A skin lesion imaged with a dermatoscope.
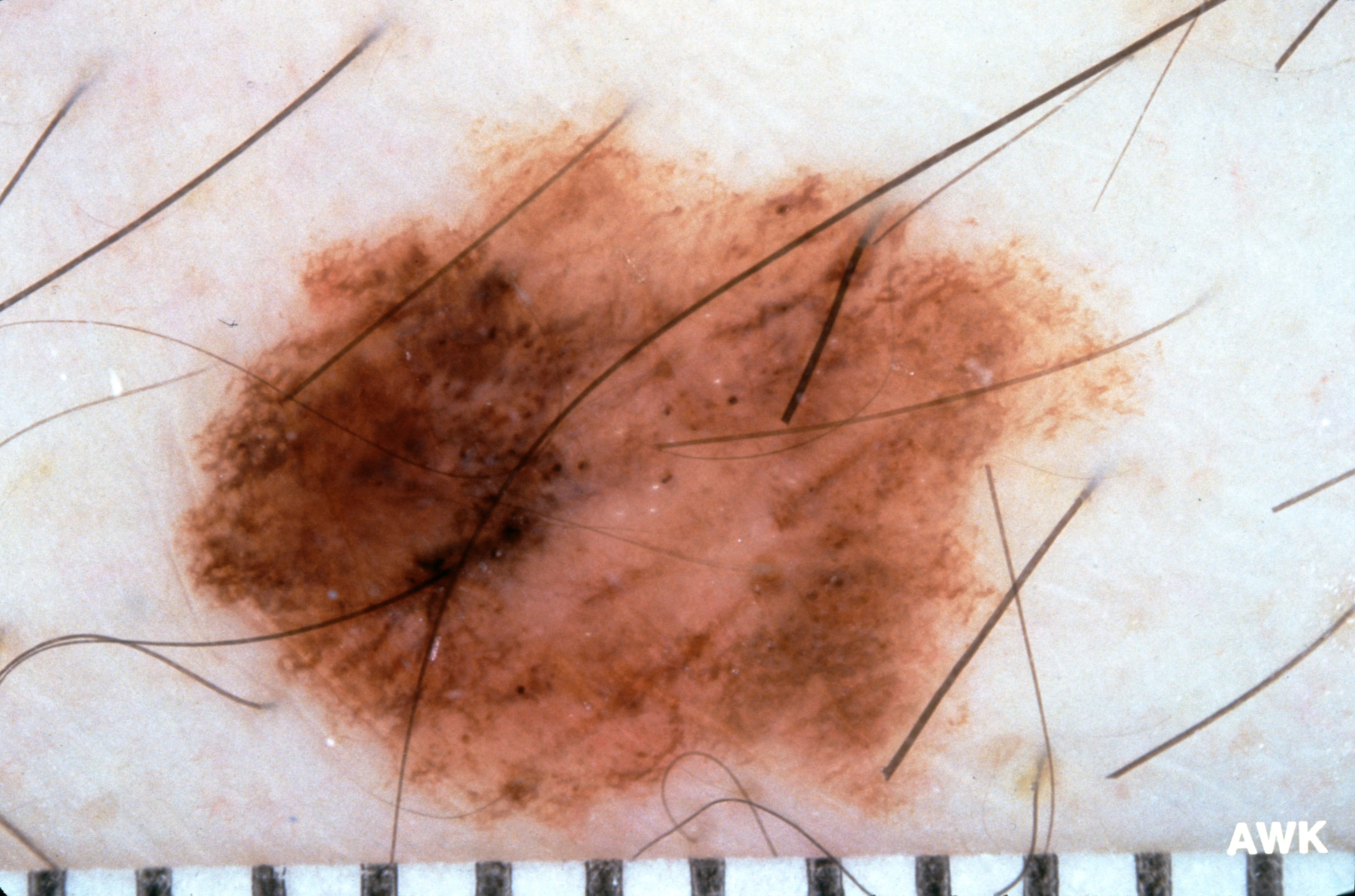Case summary:
On dermoscopy, the lesion shows pigment network and milia-like cysts. A large lesion occupying much of the field. The lesion's extent is x1=180 y1=112 x2=1143 y2=854.
Conclusion:
On biopsy, the diagnosis was a melanoma.